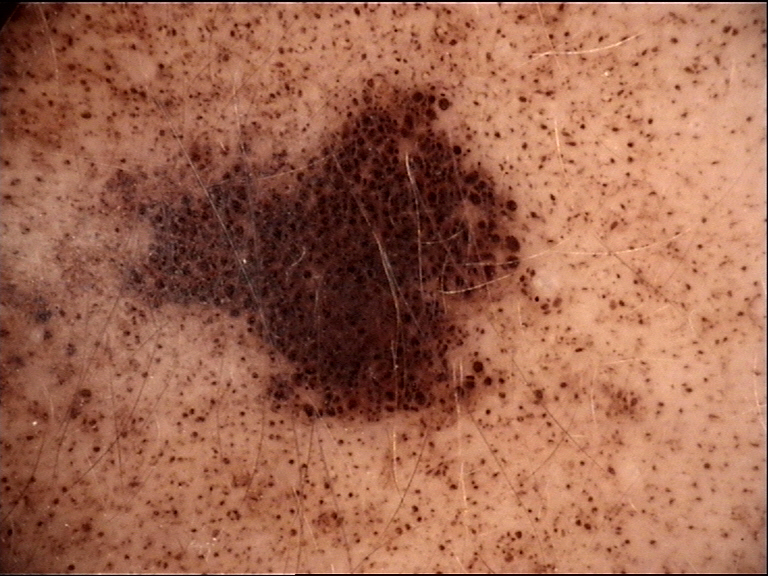A dermoscopy image of a single skin lesion.
The architecture is that of a banal lesion.
The diagnosis was a congenital compound nevus.